A female subject age 78; a clinical close-up of a skin lesion; acquired for a research image collection, with no referral diagnosis; on a questionnaire the patient reported no prior organ transplant and no personal history of cancer; the patient describes having numerous moles; the patient says their skin tans without first burning.
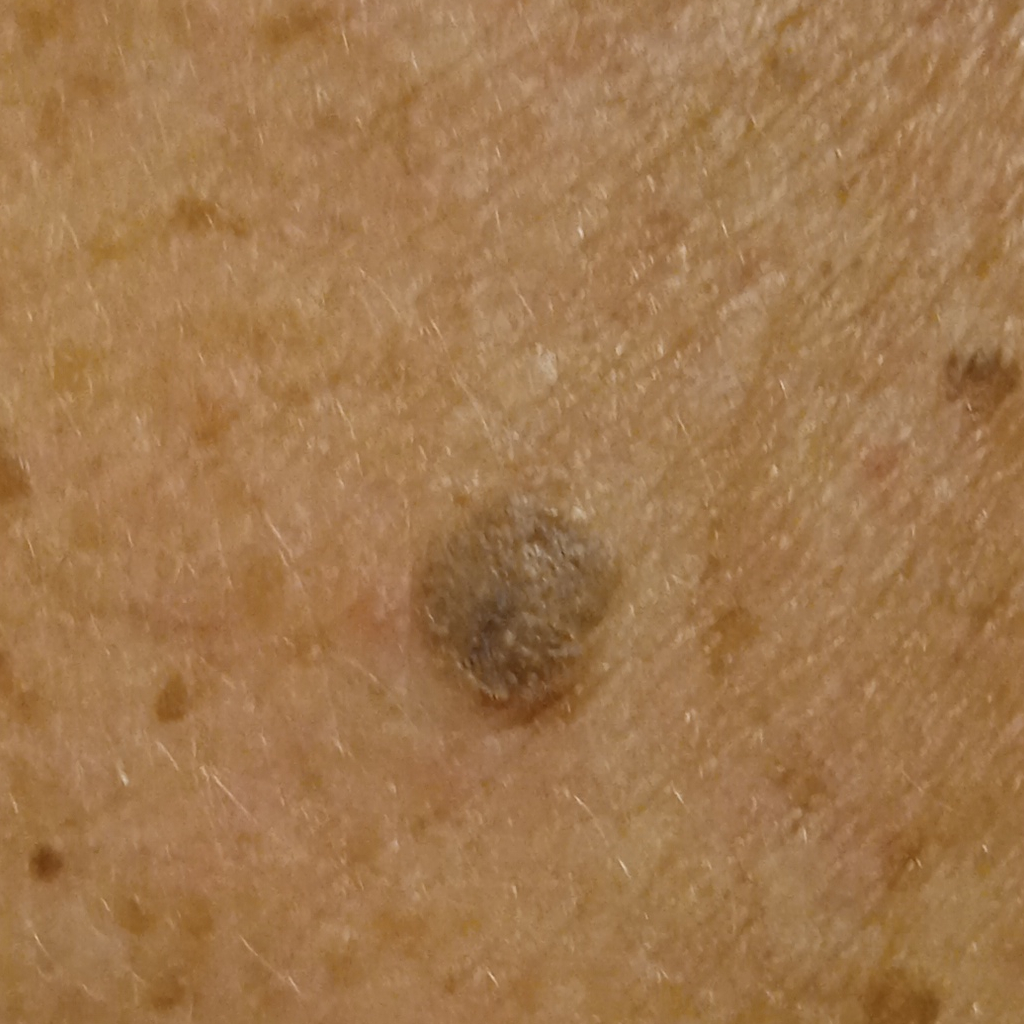| feature | finding |
|---|---|
| body site | the back |
| size | 7.3 mm |
| diagnosis | seborrheic keratosis (dermatologist consensus) |